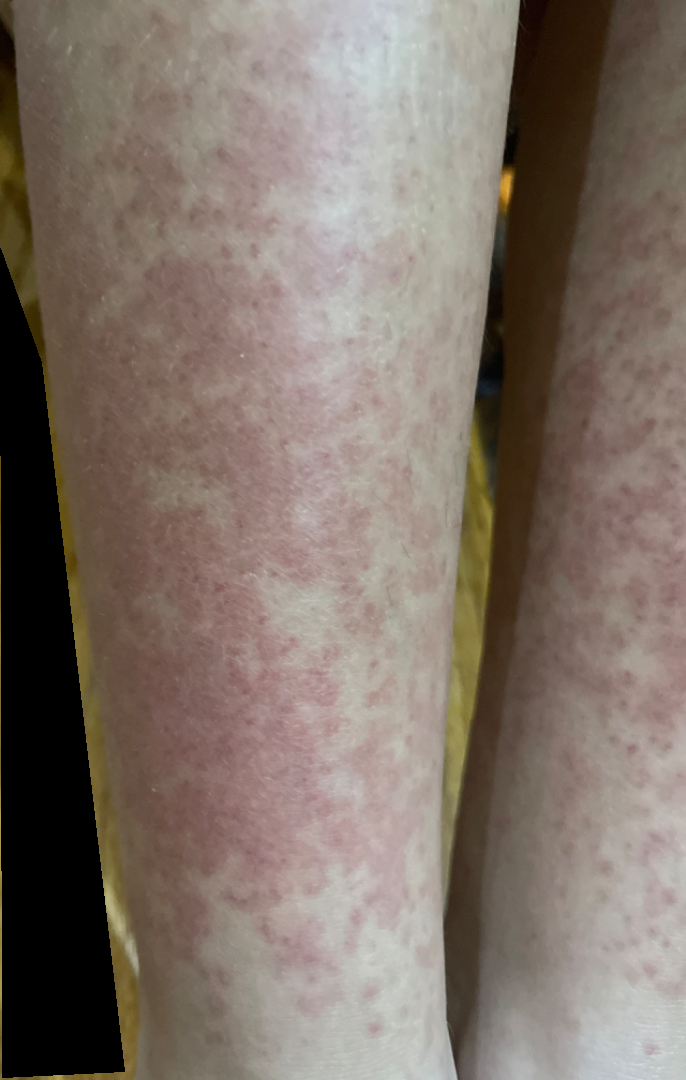On photographic review by a dermatologist: Drug Rash (favored); Viral Exanthem (possible); Leukocytoclastic Vasculitis (remote).